A male subject aged around 70; a dermoscopic view of a skin lesion — 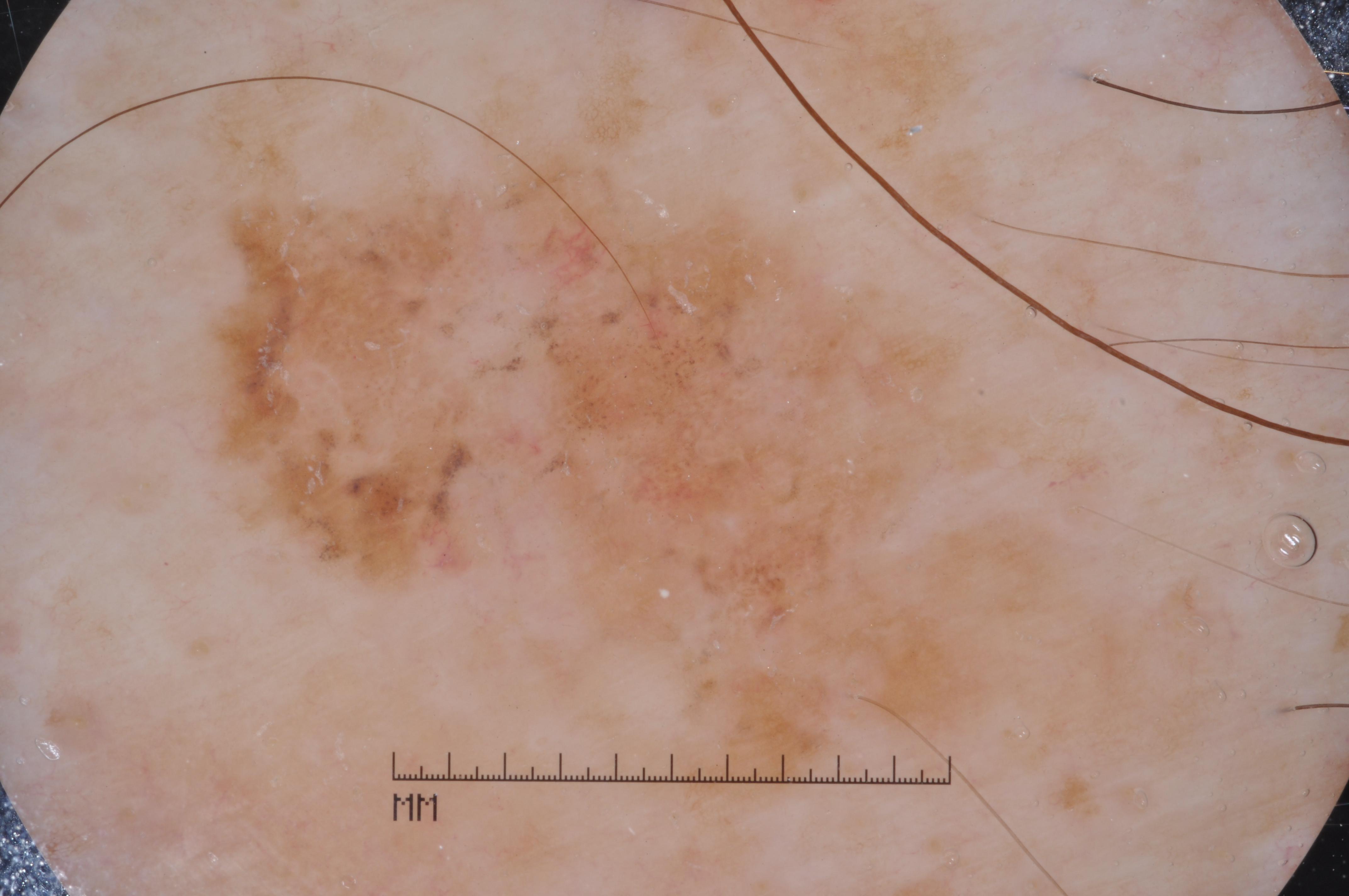{
  "lesion_extent": {
    "approx_field_fraction_pct": 46
  },
  "lesion_location": {
    "bbox_xyxy": [
      174,
      22,
      1106,
      834
    ]
  },
  "dermoscopic_features": {
    "present": [
      "milia-like cysts",
      "pigment network",
      "negative network"
    ],
    "absent": [
      "streaks"
    ]
  },
  "diagnosis": {
    "name": "melanoma",
    "malignancy": "malignant",
    "lineage": "melanocytic",
    "provenance": "histopathology"
  }
}